A dermoscopic close-up of a skin lesion: 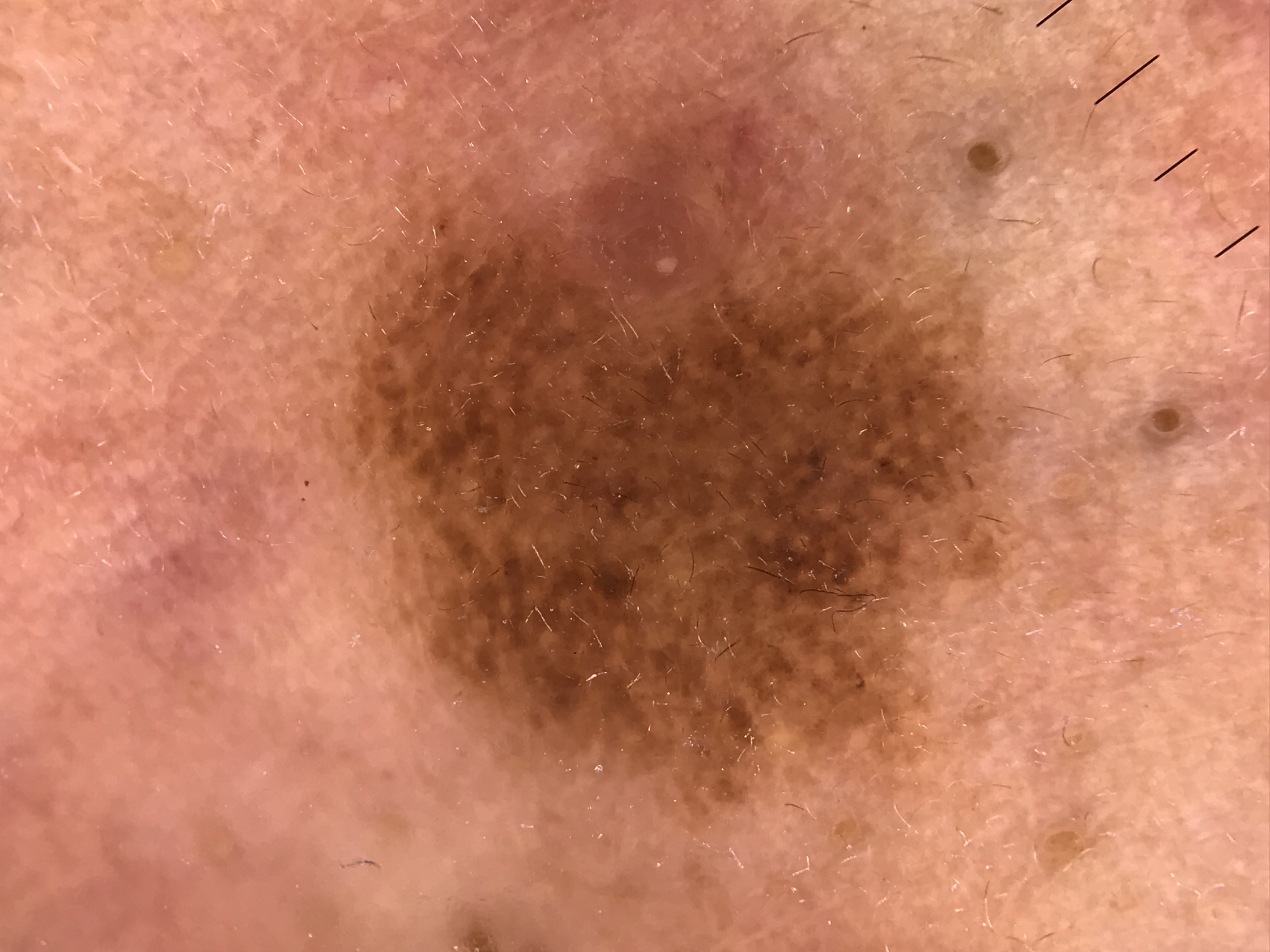The diagnosis was a compound nevus.